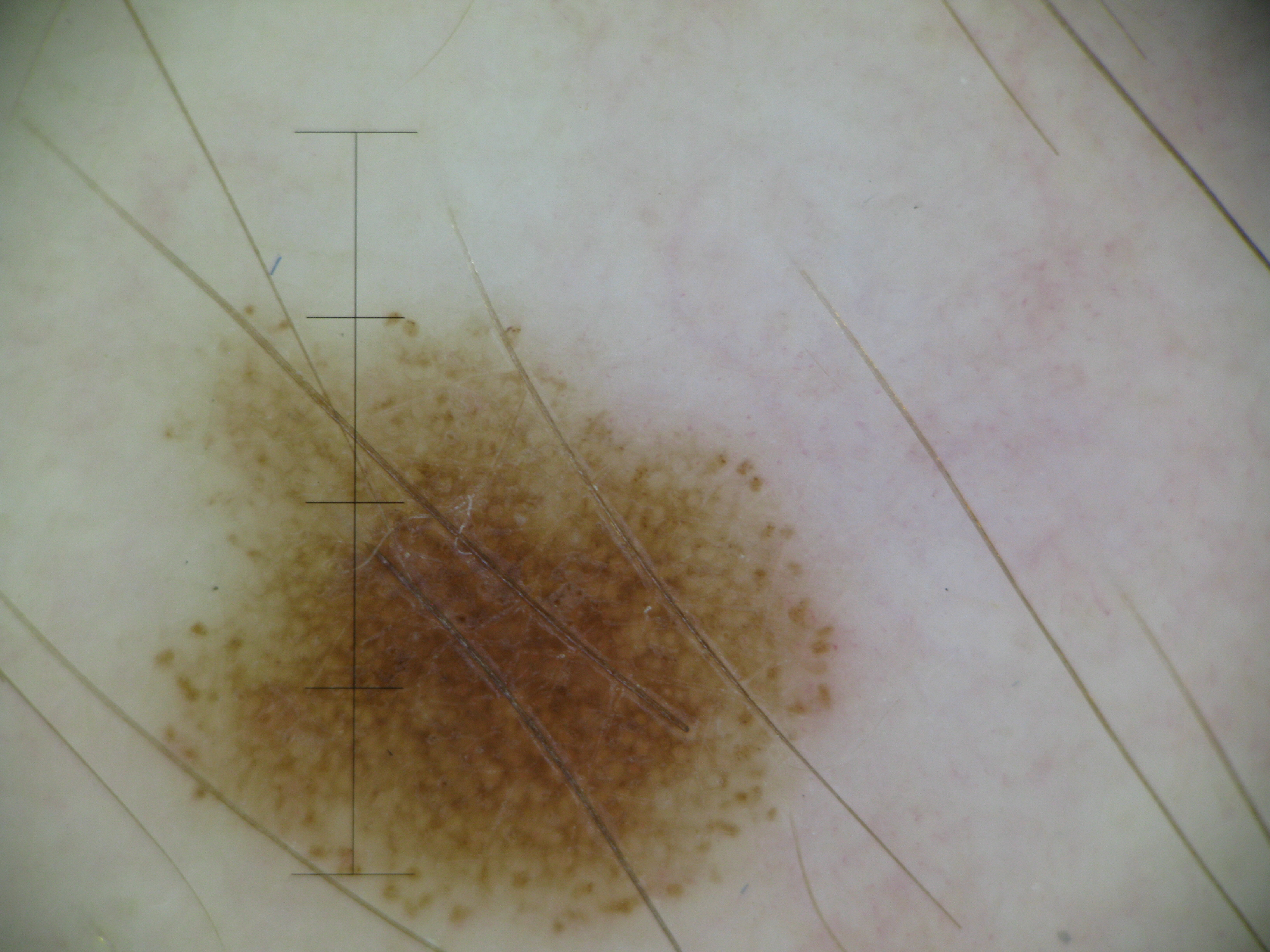Findings: A dermoscopic image of a skin lesion. Conclusion: Consistent with a dysplastic junctional nevus.